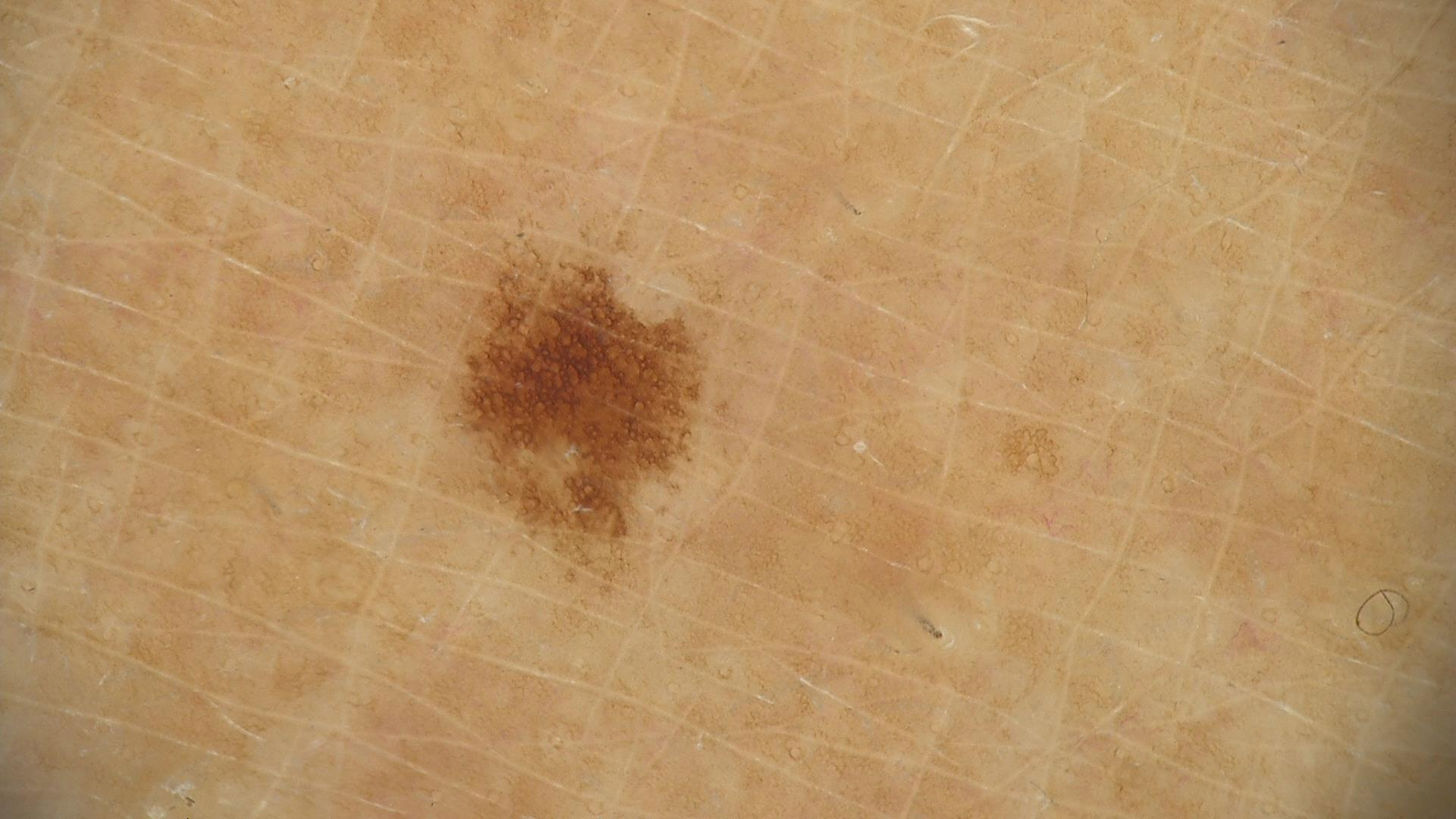Case:
- label · dysplastic junctional nevus (expert consensus)